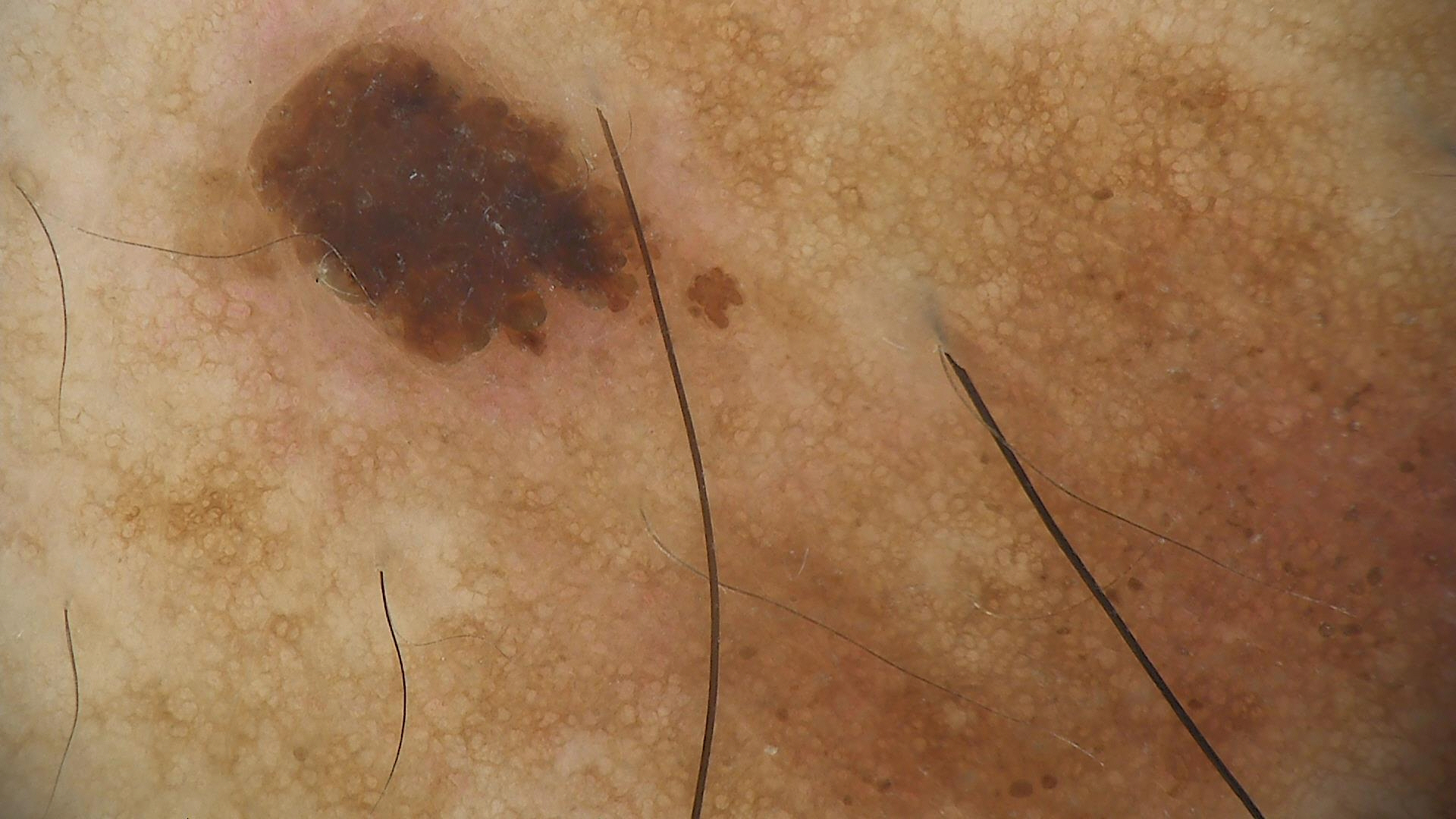lesion type=keratinocytic; class=seborrheic keratosis (expert consensus).